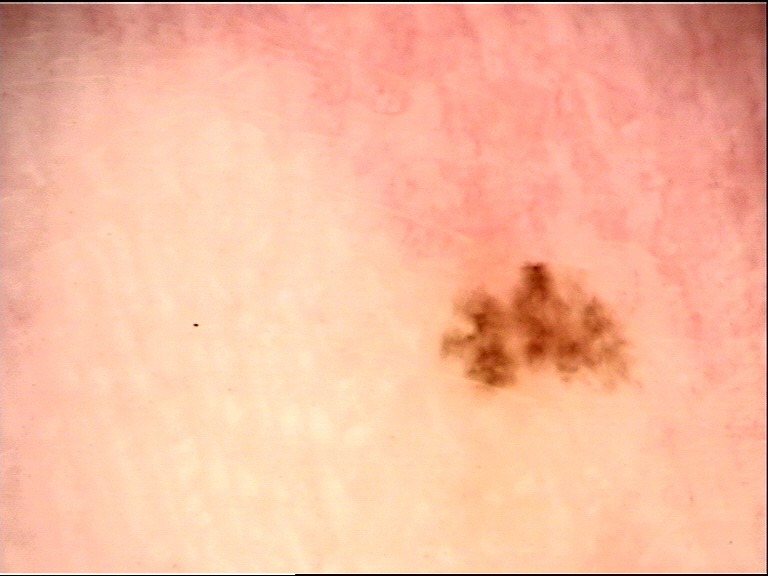Consistent with an acral dysplastic junctional nevus.